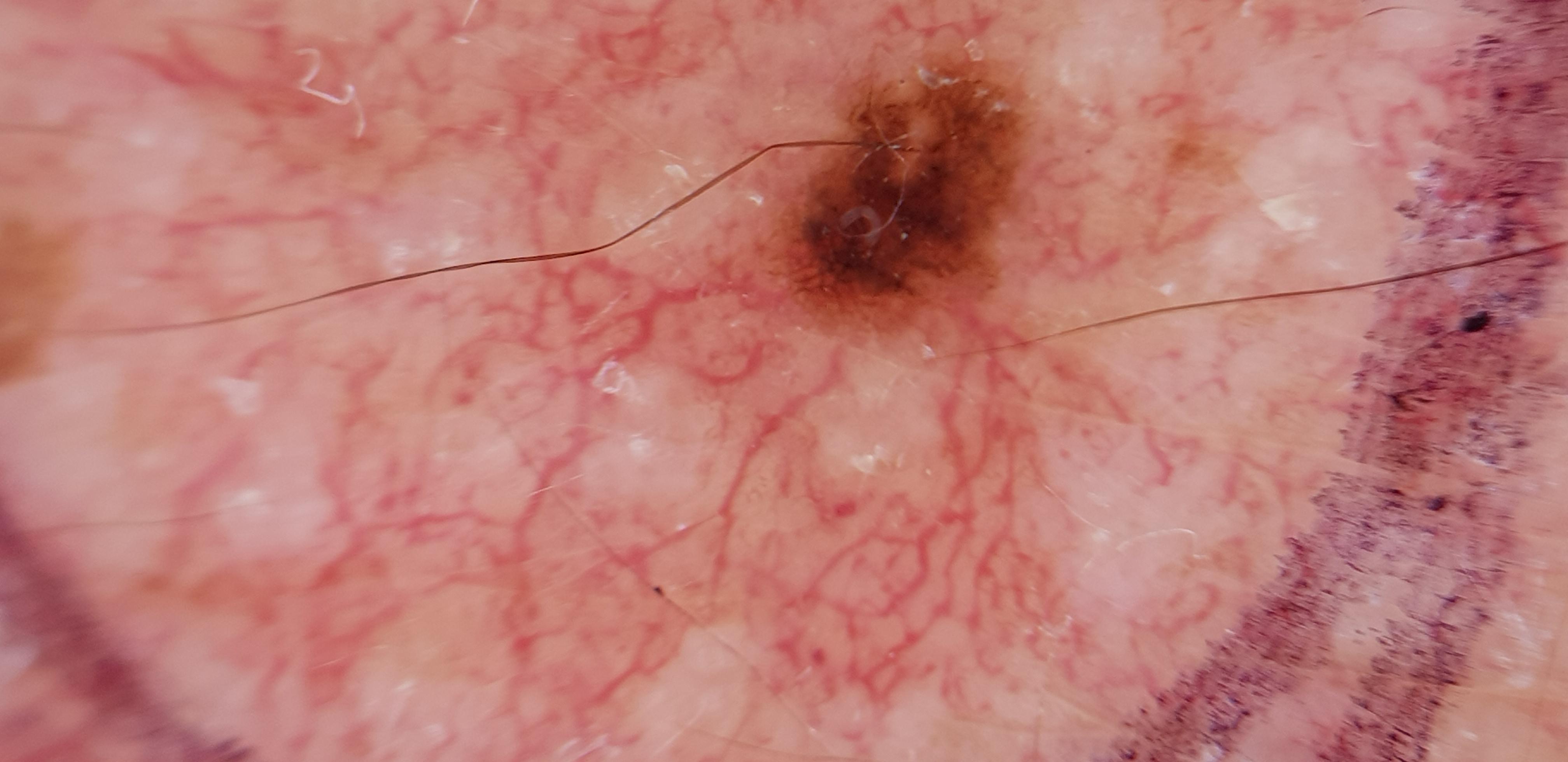Clinical context:
A male subject aged 73 to 77. A skin lesion imaged with a dermatoscope.
Conclusion:
Biopsy-confirmed as a benign lesion — a nevus.